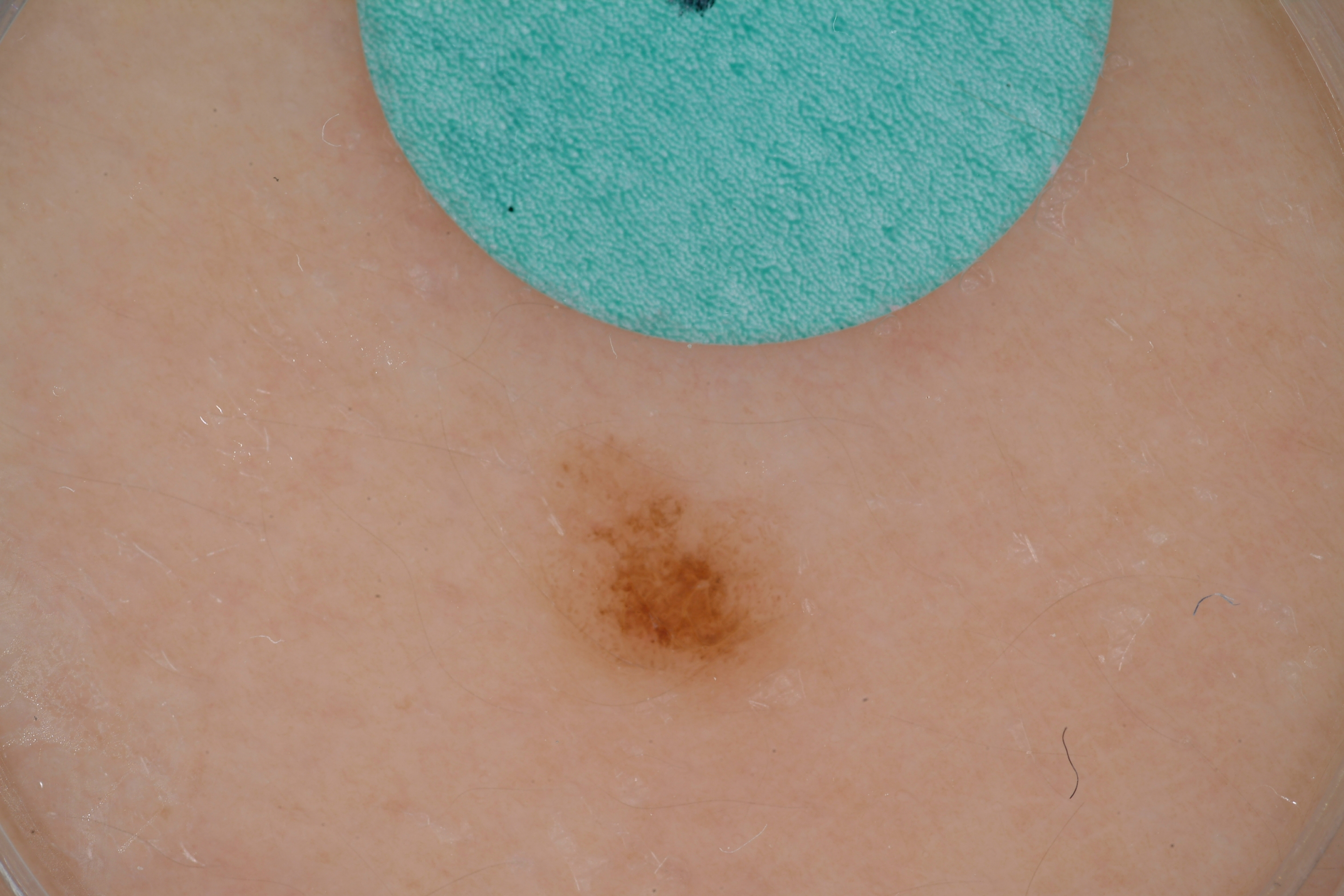image type = dermoscopic image; lesion extent = small; lesion location = (517, 417, 805, 682); features = globules; impression = a benign lesion.